A dermoscopic image of a skin lesion.
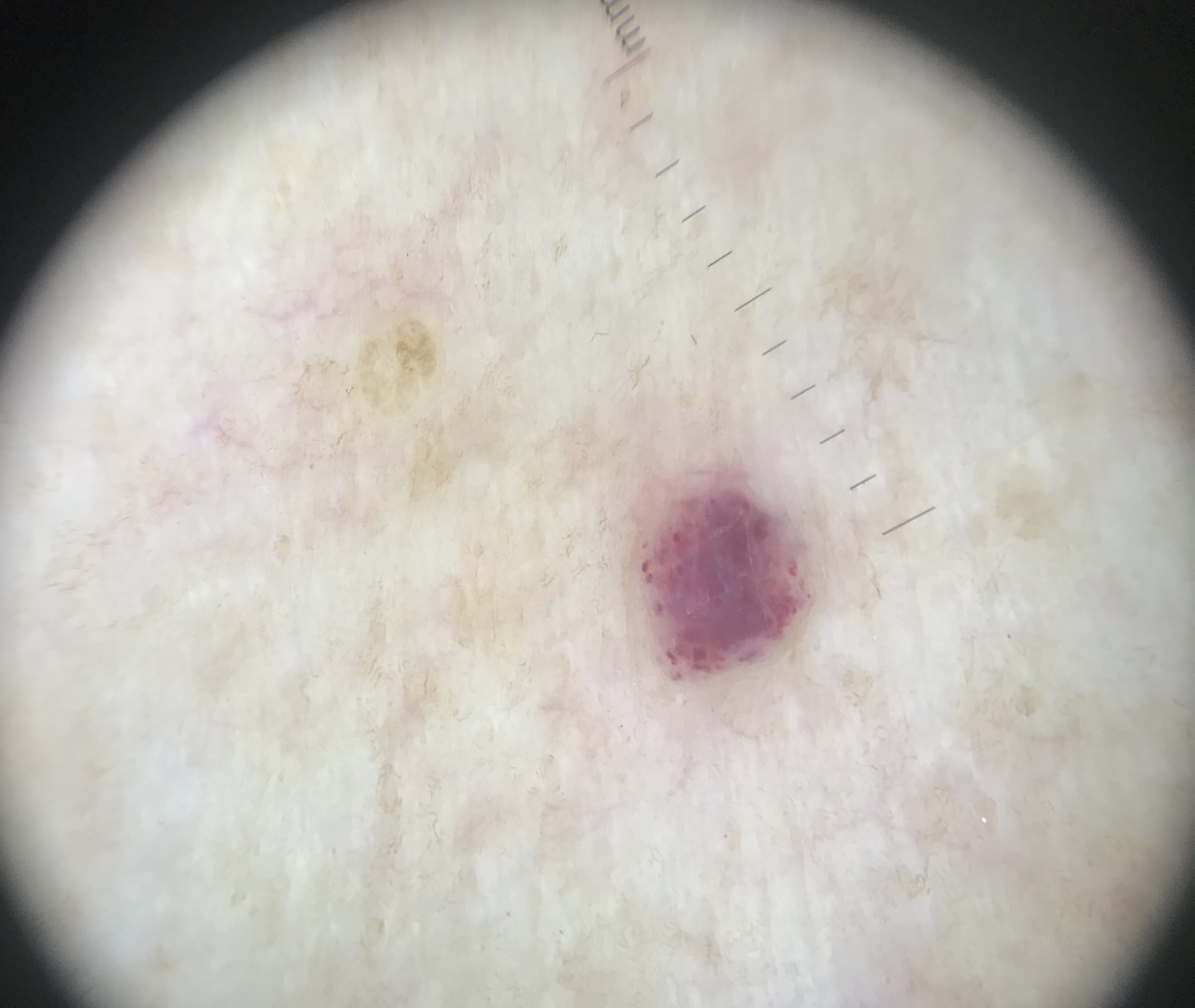label — hemangioma (expert consensus)